A skin lesion imaged with a dermatoscope.
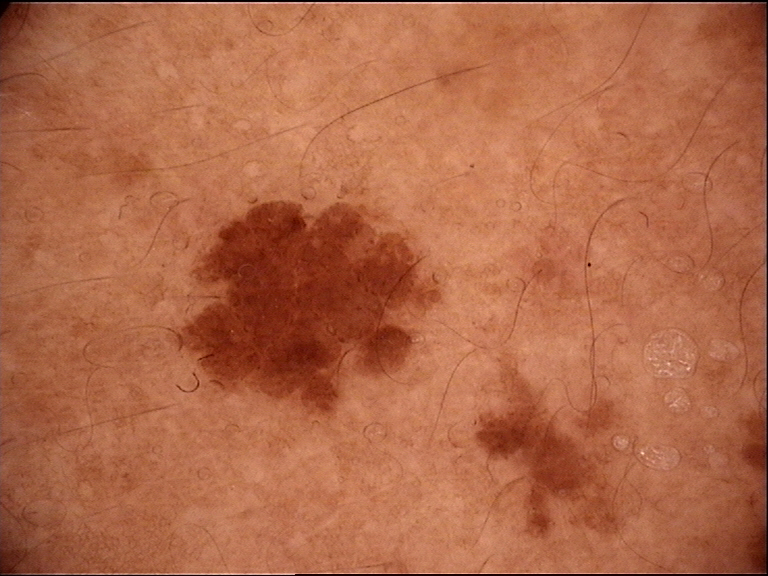diagnosis: dysplastic junctional nevus (expert consensus)